The contributor reports the lesion is rough or flaky · reported duration is less than one week · the photo was captured at an angle · the lesion involves the arm · the patient described the issue as a growth or mole · no associated systemic symptoms reported:
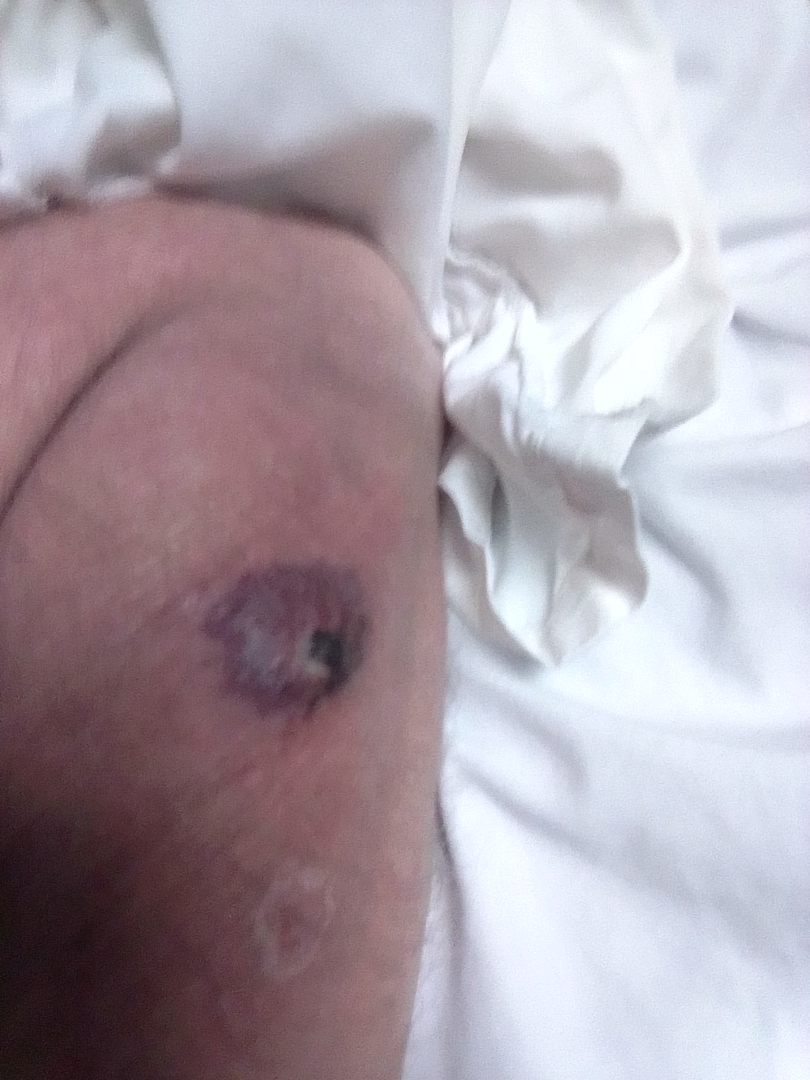assessment = ungradable on photographic review